The patient says their skin reddens painfully with sun exposure · referred with a clinical suspicion of melanoma · a female subject 50 years old · a dermoscopic image of a skin lesion: 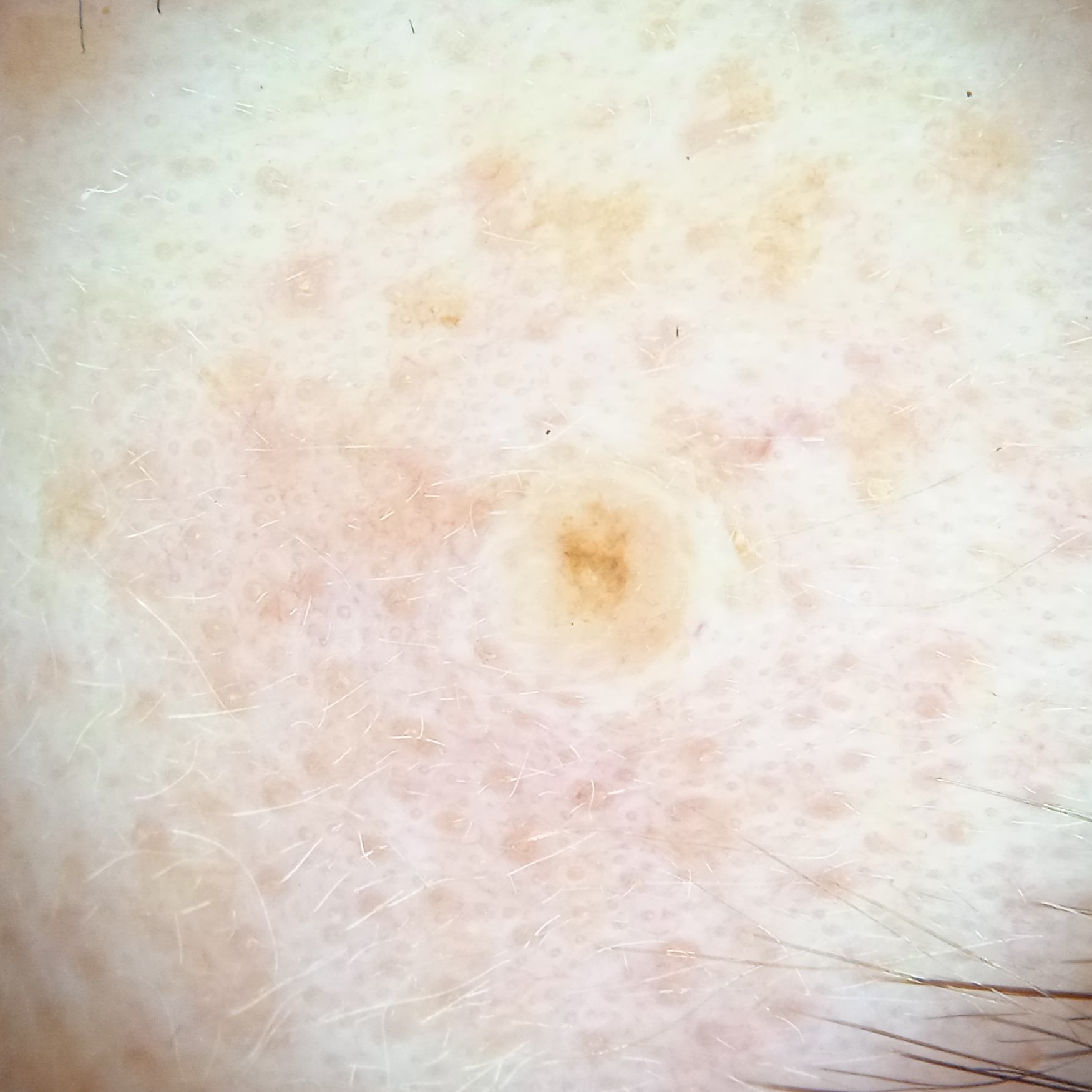Located on the face. The lesion is about 1.8 mm across. The lesion was assessed as a melanocytic nevus.